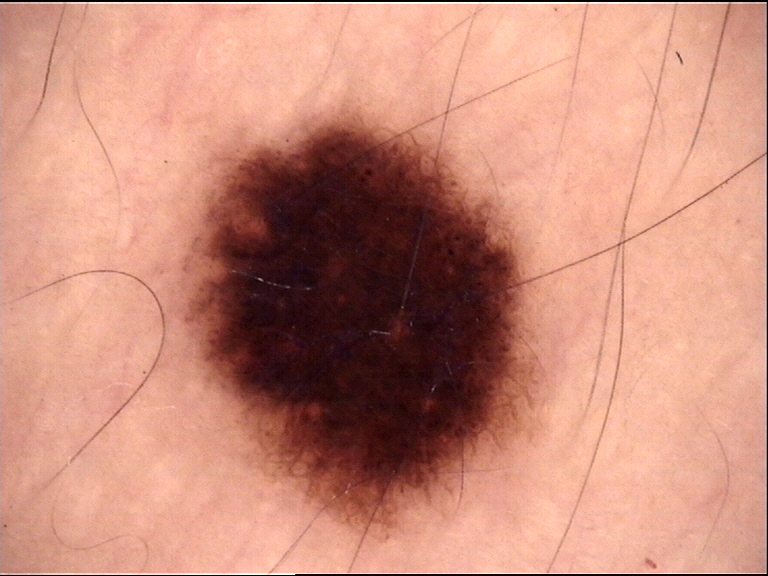  image: dermatoscopy
  diagnosis:
    name: dysplastic junctional nevus
    code: jd
    malignancy: benign
    super_class: melanocytic
    confirmation: expert consensus